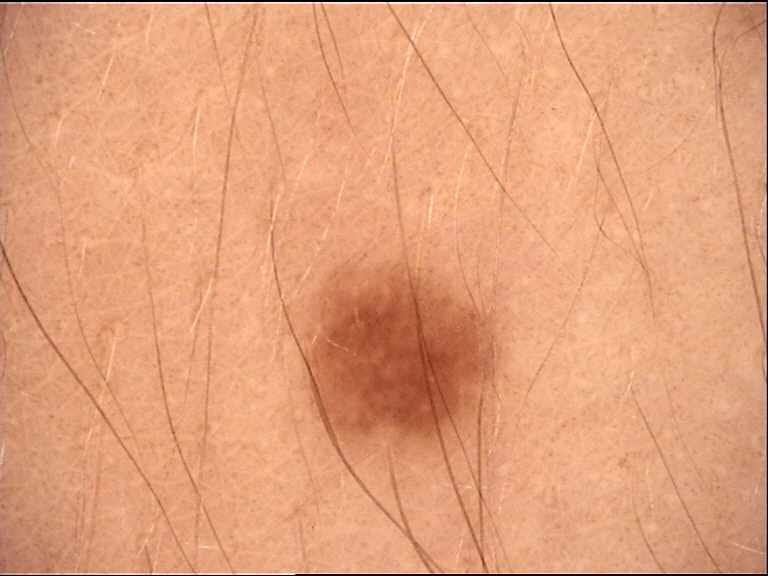diagnosis = junctional nevus (expert consensus).